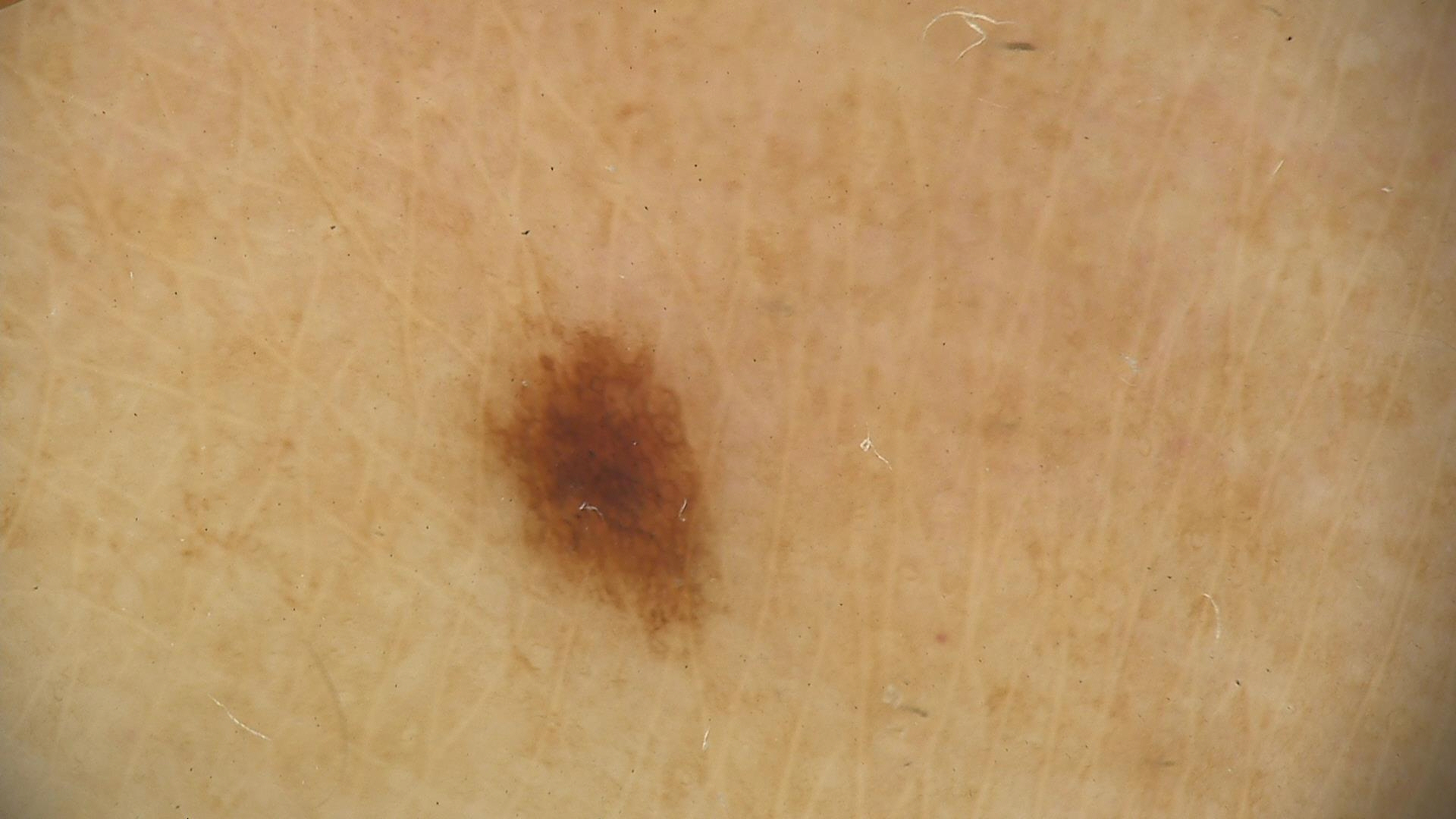  image: dermatoscopy
  diagnosis:
    name: dysplastic junctional nevus
    code: jd
    malignancy: benign
    super_class: melanocytic
    confirmation: expert consensus